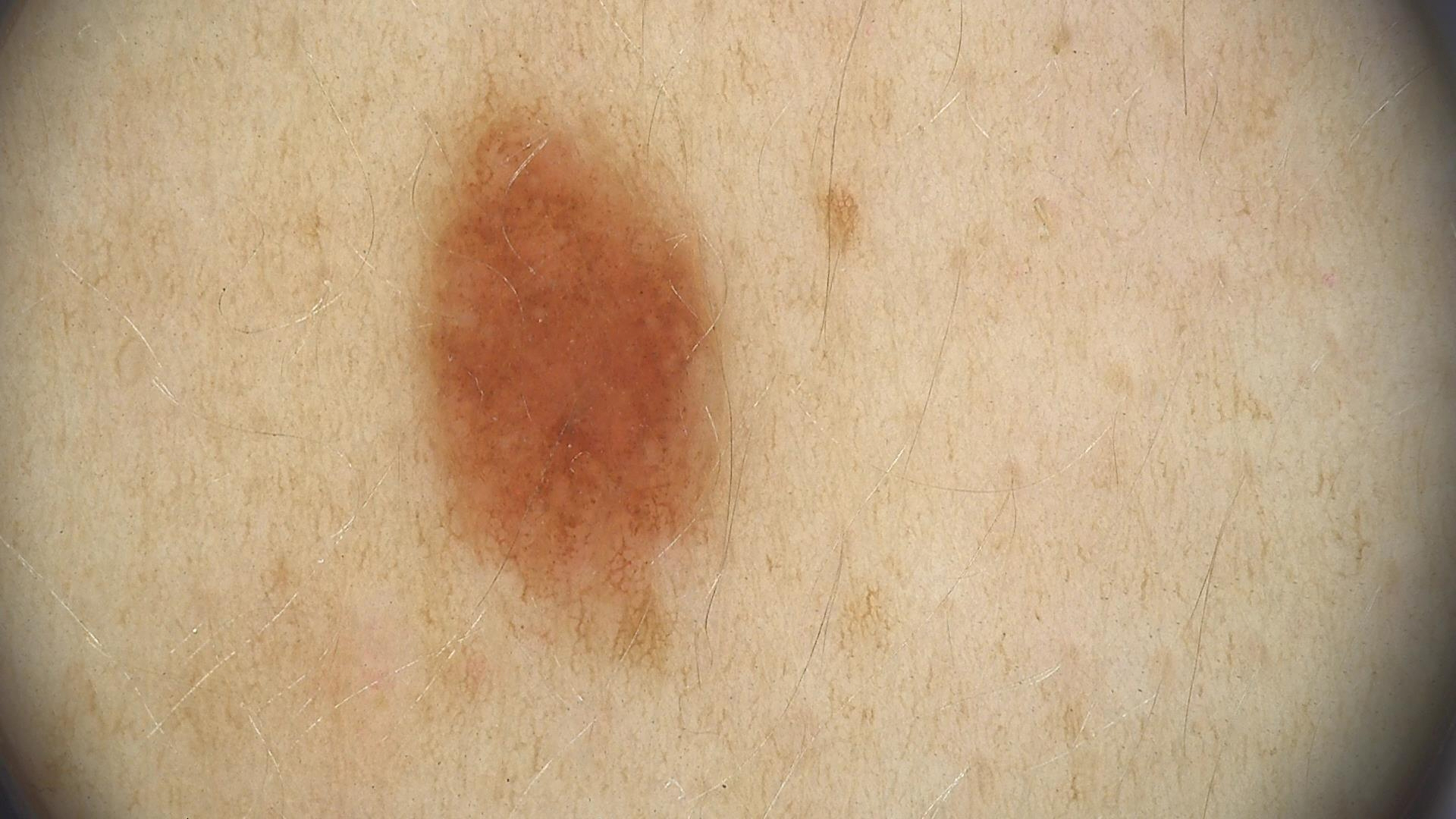A skin lesion imaged with a dermatoscope. Labeled as a benign lesion — a dysplastic junctional nevus.